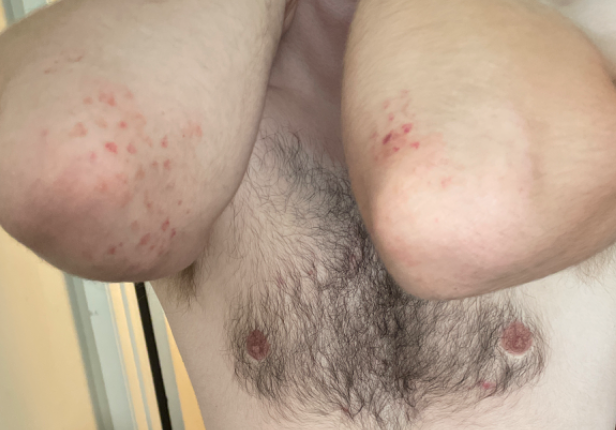Case summary:
- present for — three to twelve months
- contributor — male, age 18–29
- lesion symptoms — enlargement, pain, burning, darkening, itching, bothersome appearance and bleeding
- systemic symptoms — shortness of breath, chills and fatigue
- view — at a distance
- self-categorized as — a rash
- texture — flat
- differential diagnosis — Contact dermatitis and Purpura were considered with similar weight; a more distant consideration is Pigmented purpuric eruption; less likely is ecchymoses